A dermoscopy image of a single skin lesion.
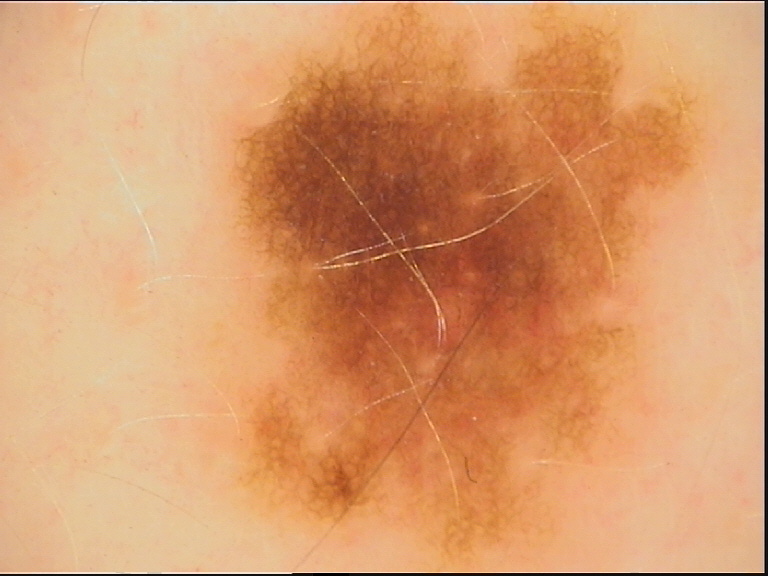label — dysplastic junctional nevus (expert consensus)